This image was taken at a distance · the lesion involves the arm and palm — 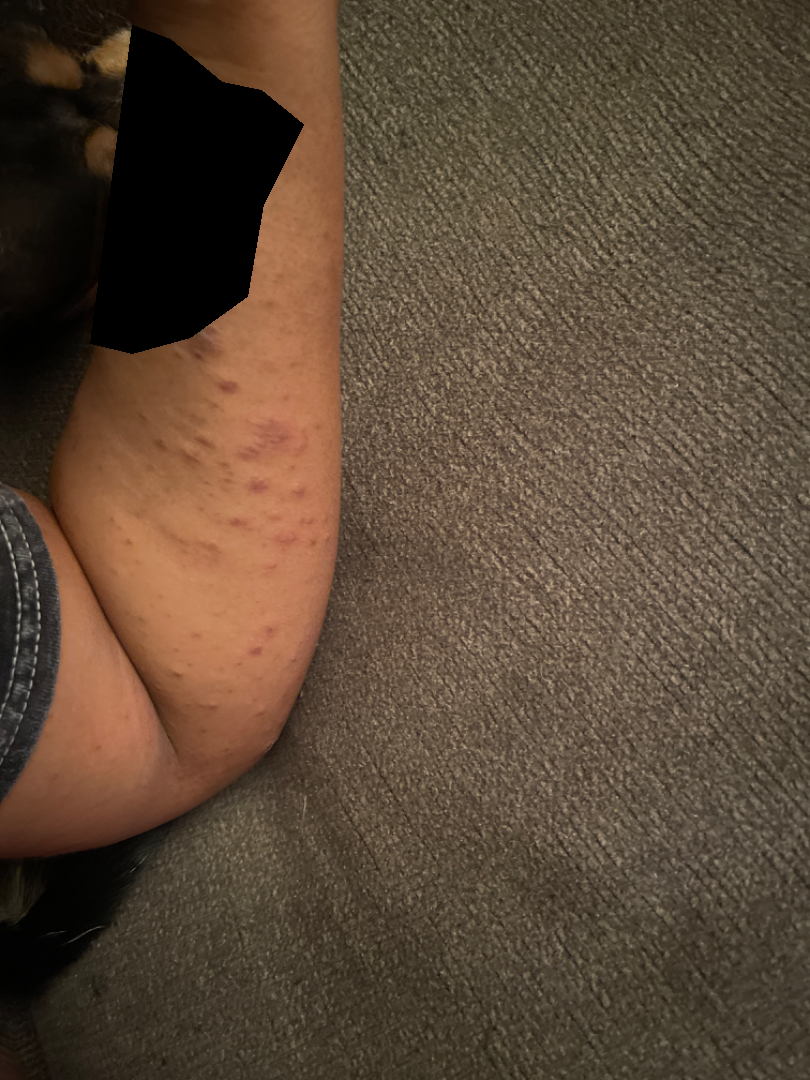The leading impression is Pityriasis lichenoides; with consideration of Psoriasis.